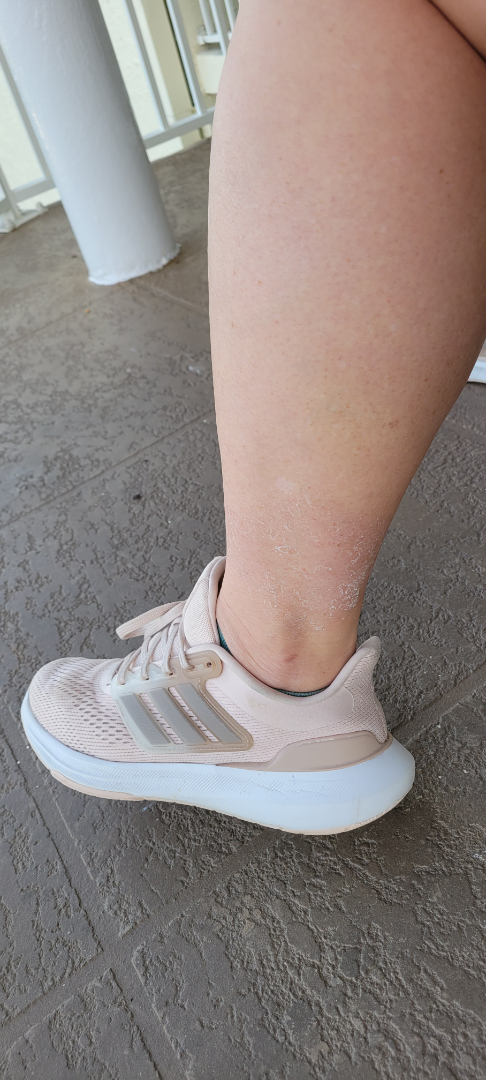described texture: rough or flaky
contributor: female, age 50–59
view: at a distance
lesion symptoms: enlargement and bothersome appearance
symptom duration: more than one year
other reported symptoms: none reported
affected area: leg
self-categorized as: a rash
impression: most consistent with Xerosis; the differential also includes Eczema; less likely is post-sunburn peeling/superficial desquamation